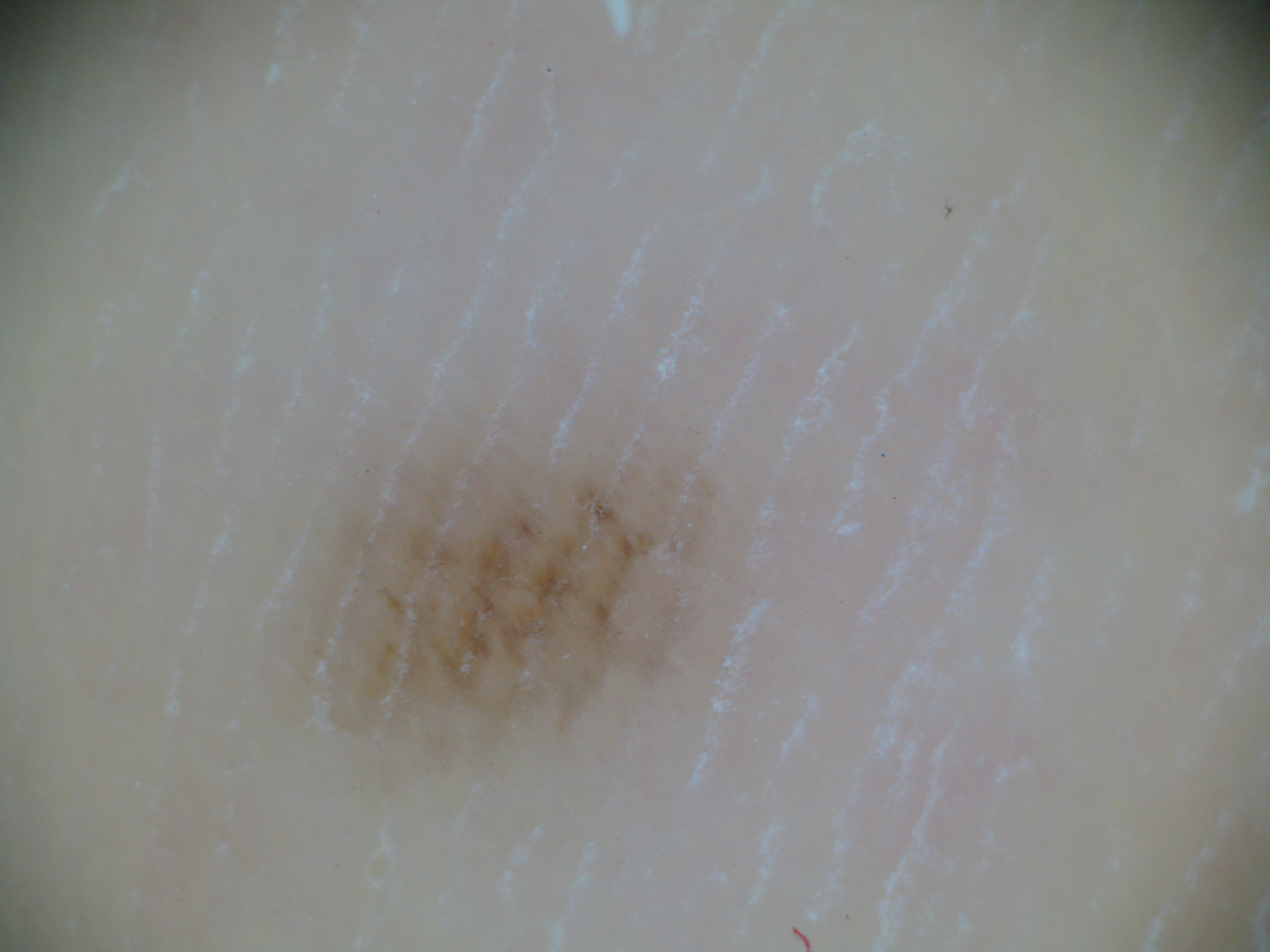A dermatoscopic image of a skin lesion. The architecture is that of a banal lesion. Consistent with an acral junctional nevus.